A dermoscopic image of a skin lesion:
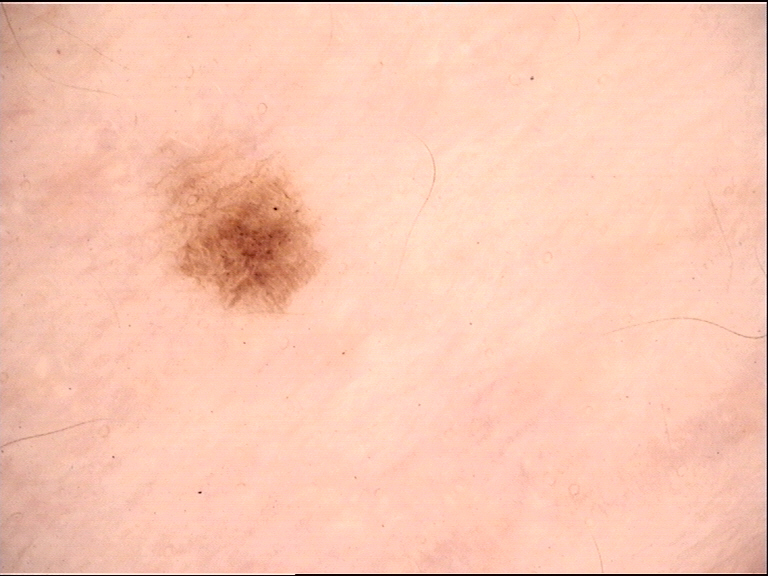Q: What is the diagnosis?
A: junctional nevus (expert consensus)